Female contributor, age 30–39 · this image was taken at an angle · the lesion involves the back of the hand, leg, head or neck, top or side of the foot and arm.
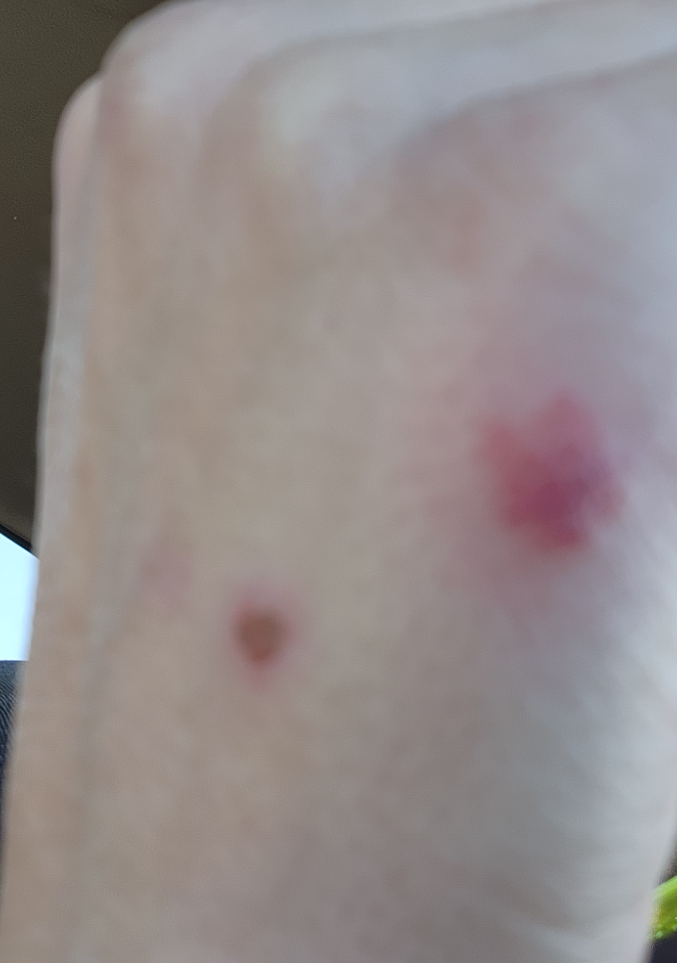Case summary:
– assessment: unable to determine